This image was taken at a distance. The patient described the issue as a rash. The affected area is the head or neck, leg, back of the hand and palm. Female contributor, age 30–39. Reported lesion symptoms include itching, bothersome appearance, pain and burning. Texture is reported as raised or bumpy. The condition has been present for less than one week. No relevant systemic symptoms.
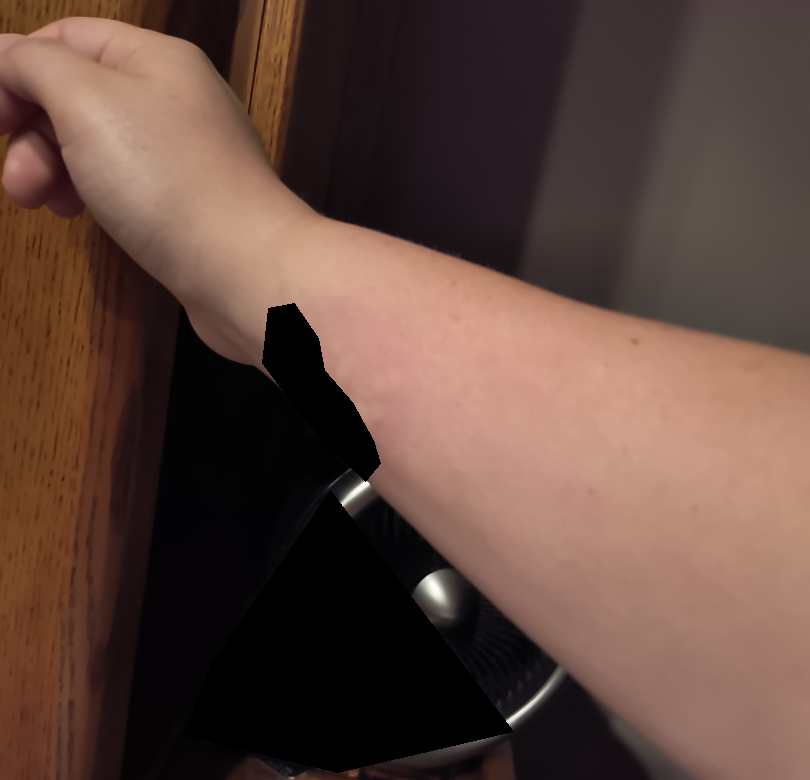diagnostic considerations — most consistent with Urticaria; the differential also includes Insect Bite; possibly Allergic Contact Dermatitis.